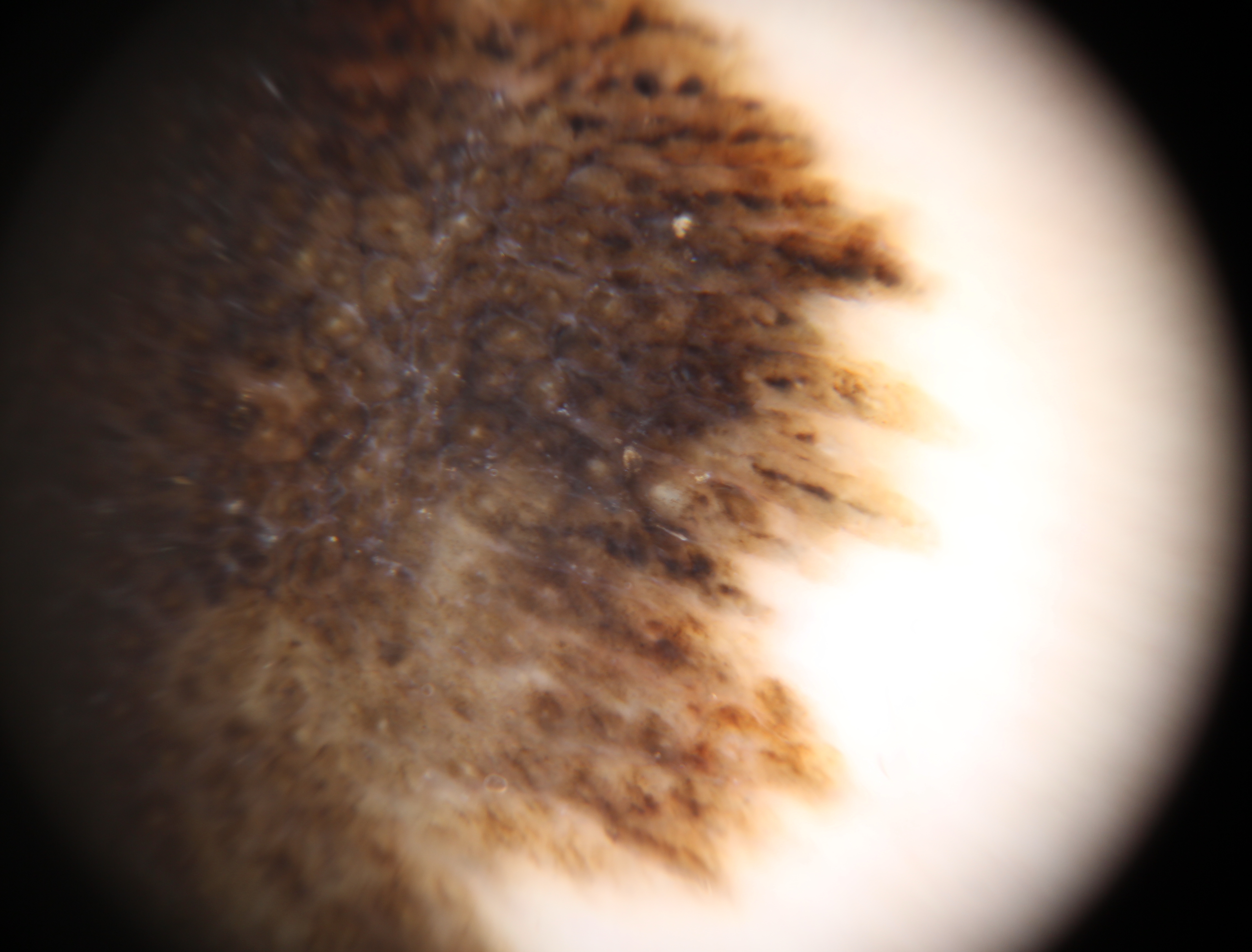Pathology: Biopsy-confirmed as a malignant lesion — an acral lentiginous melanoma.